An image taken at an angle: 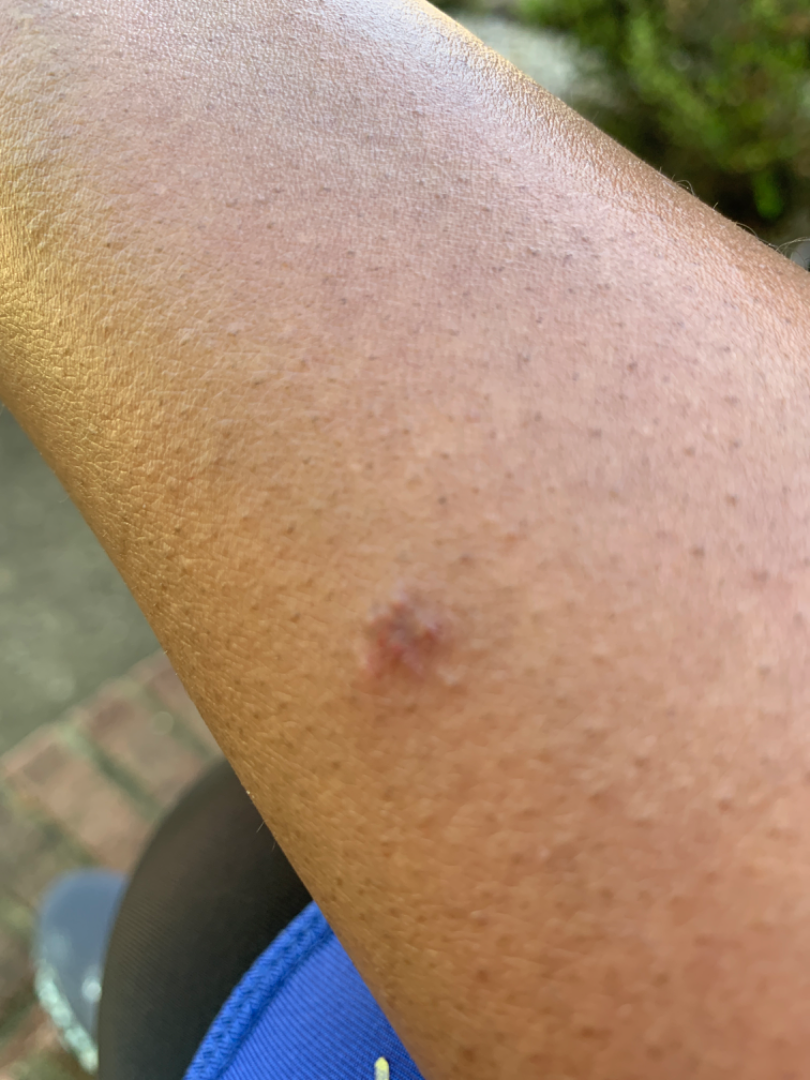assessment = not assessable
skin tone = FST V; non-clinician graders estimated Monk Skin Tone 6 (US pool) or 4 (India pool)